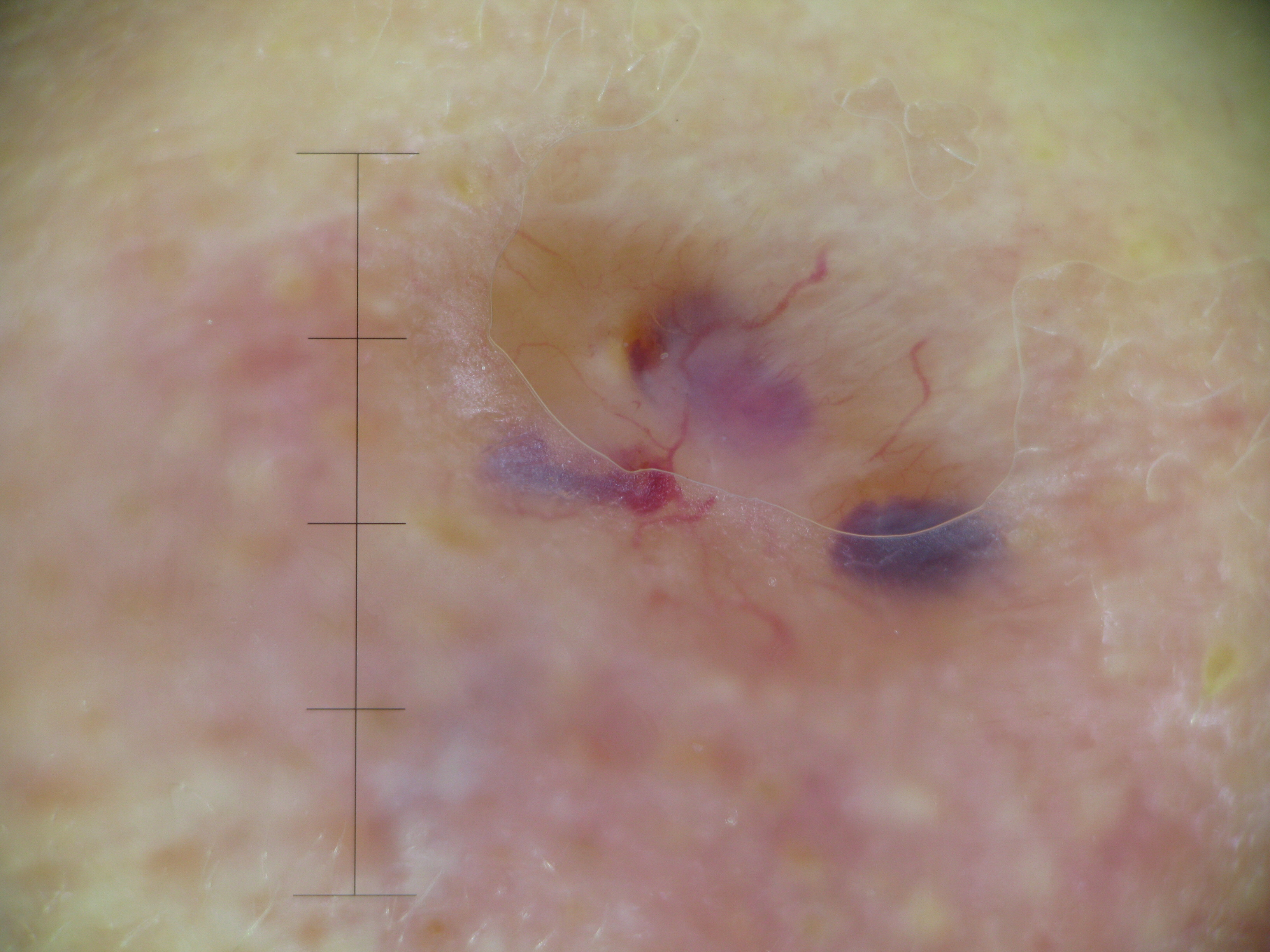– label — basal cell carcinoma (biopsy-proven)